A close-up photograph, the leg is involved: 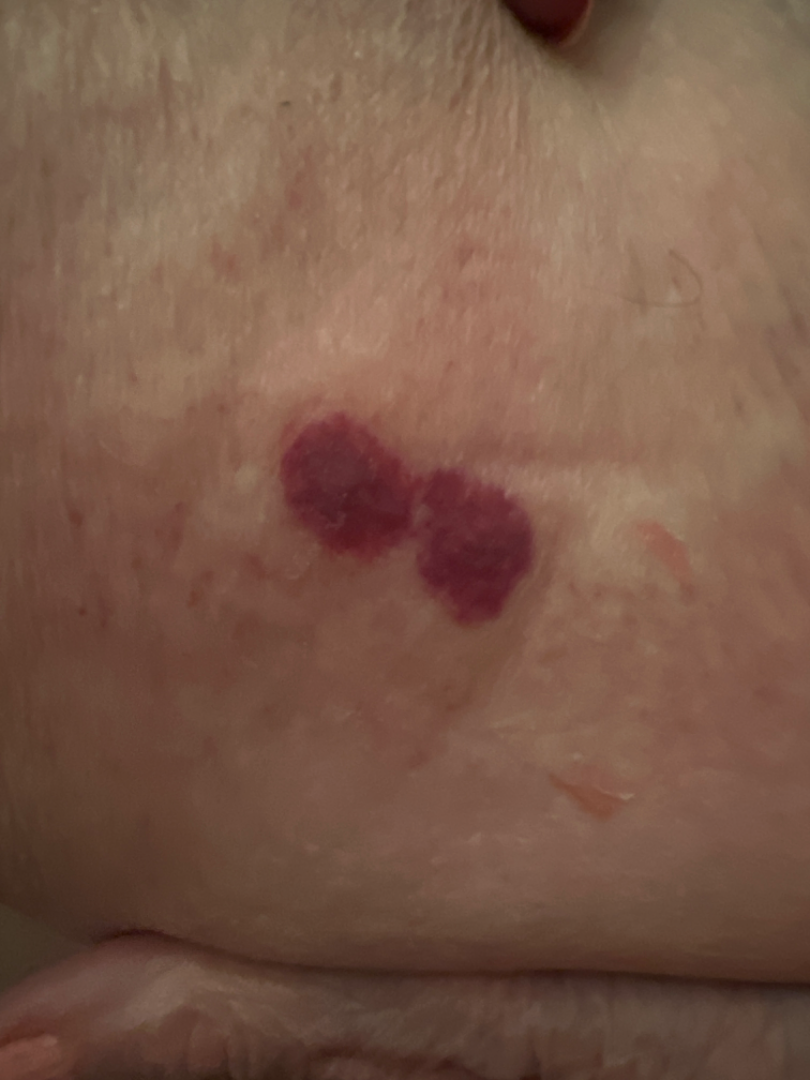Most consistent with Purpura.